A close-up photograph · located on the back of the hand · the subject is female.
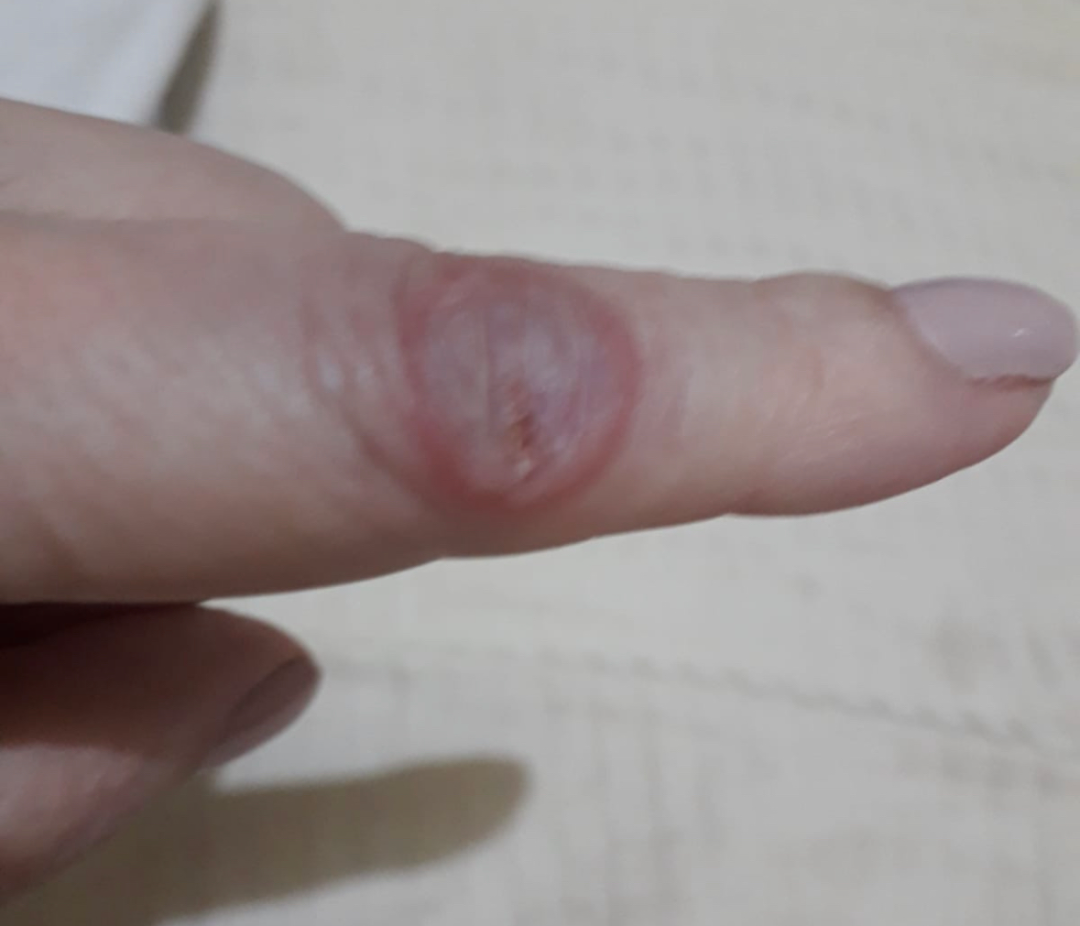assessment: not assessable.